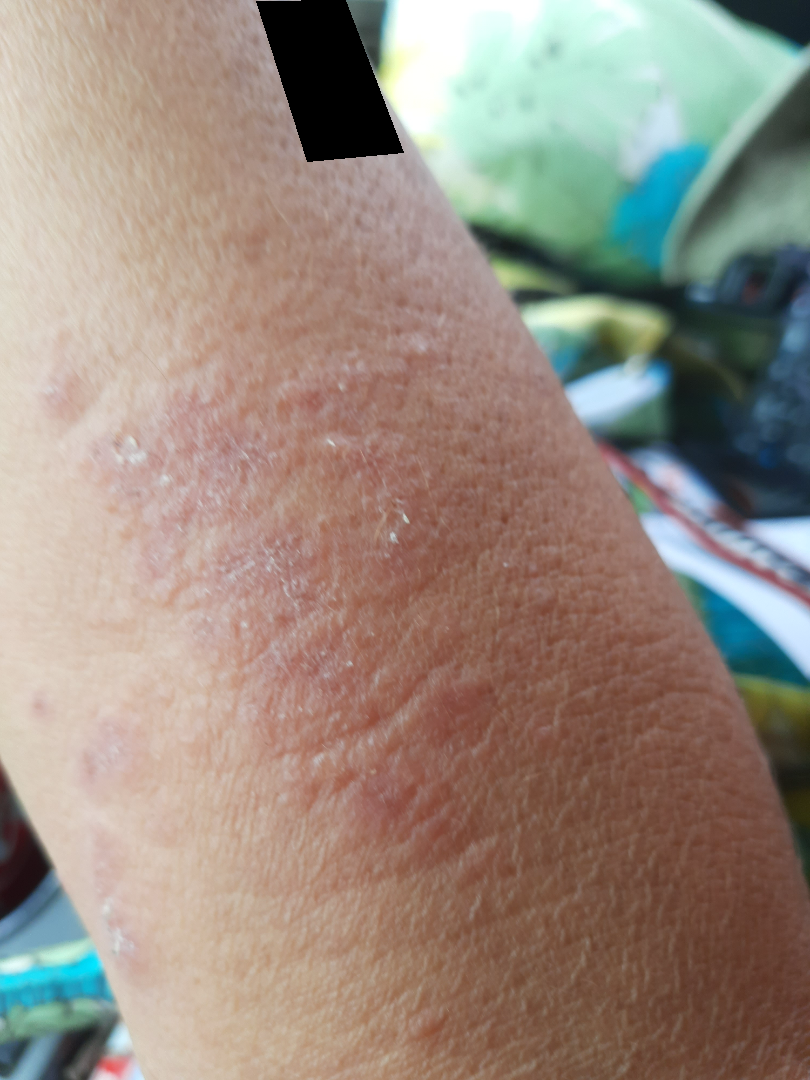<case>
  <patient_category>skin that appeared healthy to them</patient_category>
  <shot_type>at an angle</shot_type>
  <texture>rough or flaky, raised or bumpy</texture>
  <symptoms>burning, enlargement, itching</symptoms>
  <patient>female, age 60–69</patient>
  <body_site>arm, front of the torso</body_site>
  <differential>
    <leading>Chronic dermatitis, NOS</leading>
  </differential>
</case>